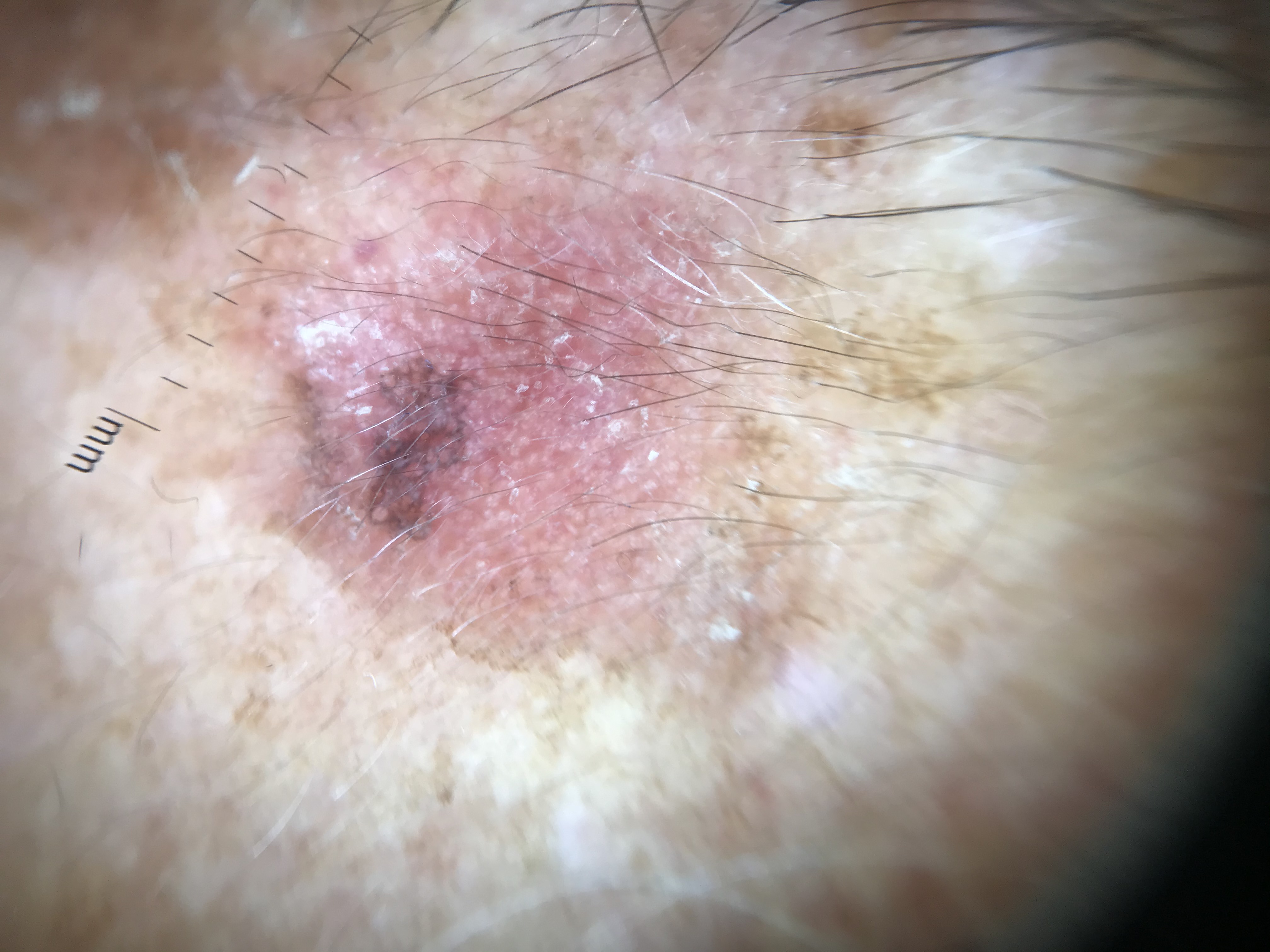diagnosis: actinic keratosis (expert consensus)